A dermoscopic close-up of a skin lesion.
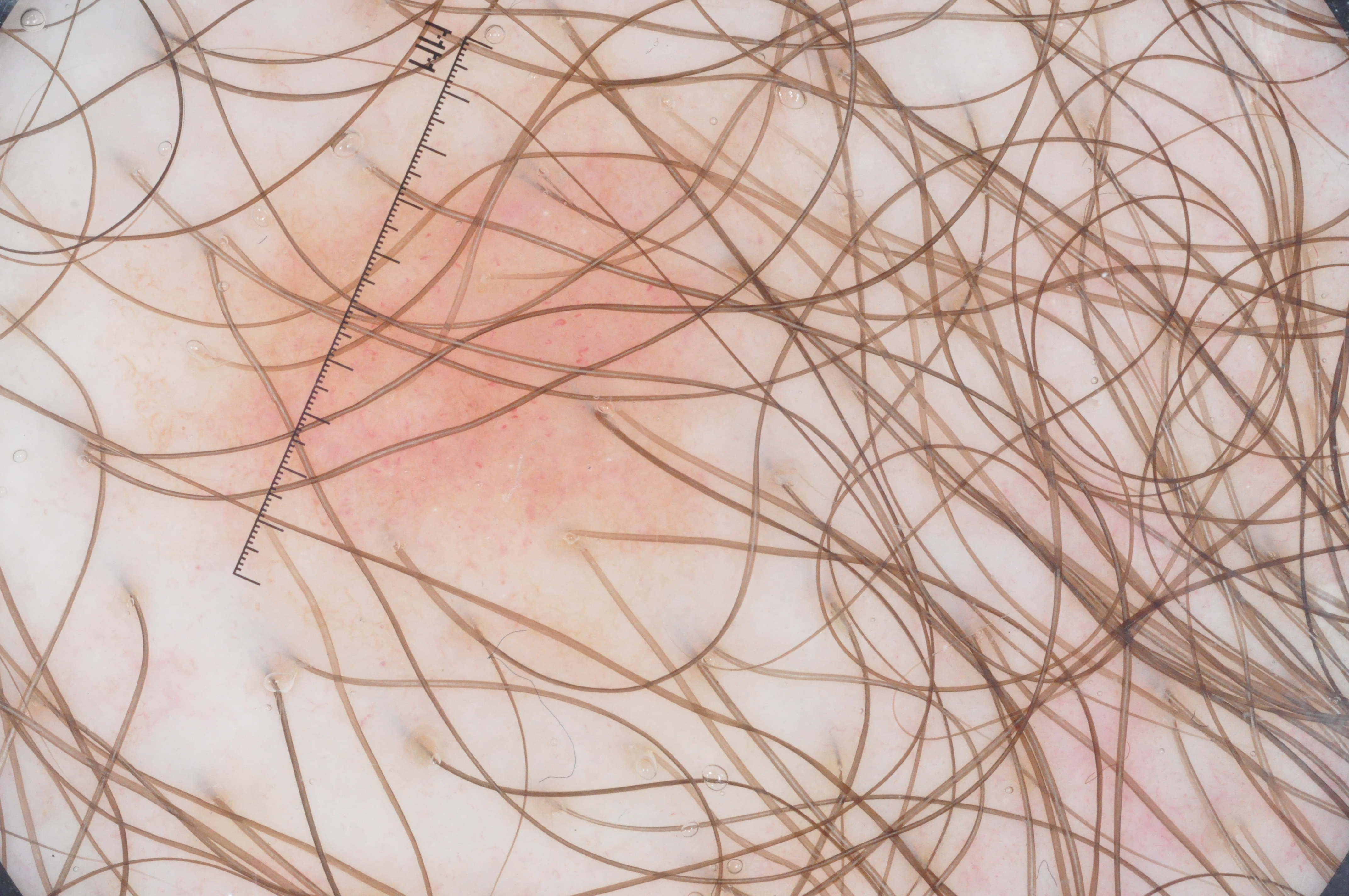Case summary:
• lesion location · x1=210, y1=67, x2=770, y2=569
• lesion size · moderate
• dermoscopic features · milia-like cysts; absent: pigment network, negative network, and streaks
• diagnosis · a melanocytic nevus, a benign lesion